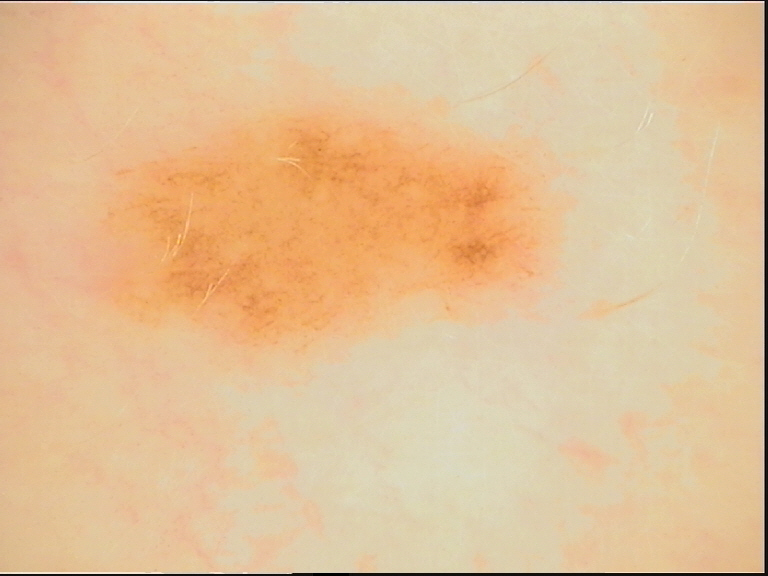image: dermoscopy; assessment: dysplastic junctional nevus (expert consensus).